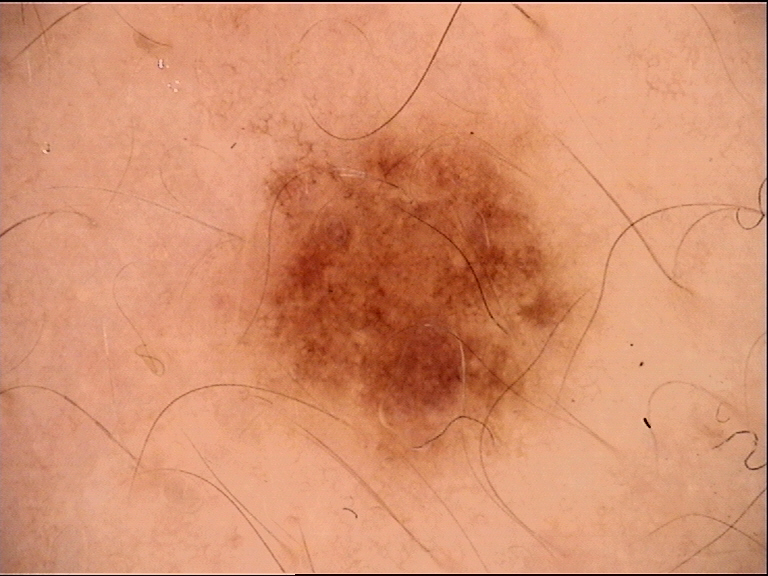Case:
Dermoscopy of a skin lesion.
Conclusion:
The diagnostic label was a benign lesion — a dysplastic junctional nevus.